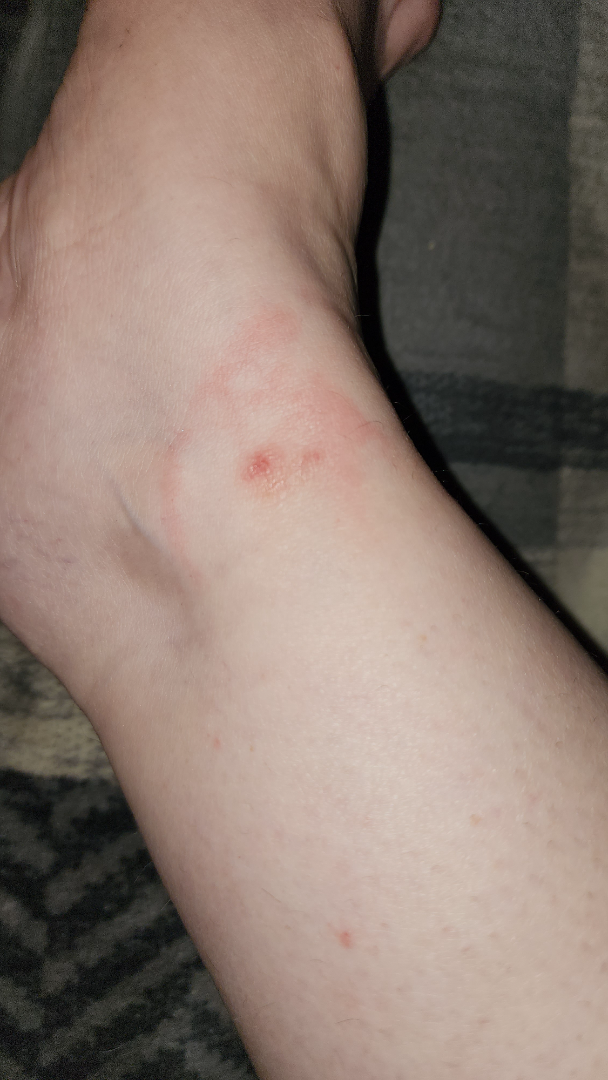On remote review of the image, Insect Bite (most likely); Allergic Contact Dermatitis (considered); Urticaria (lower probability).